Male contributor, age 40–49; the patient considered this a rash; the contributor reports the condition has been present for about one day; the lesion involves the leg; this image was taken at an angle; texture is reported as fluid-filled.
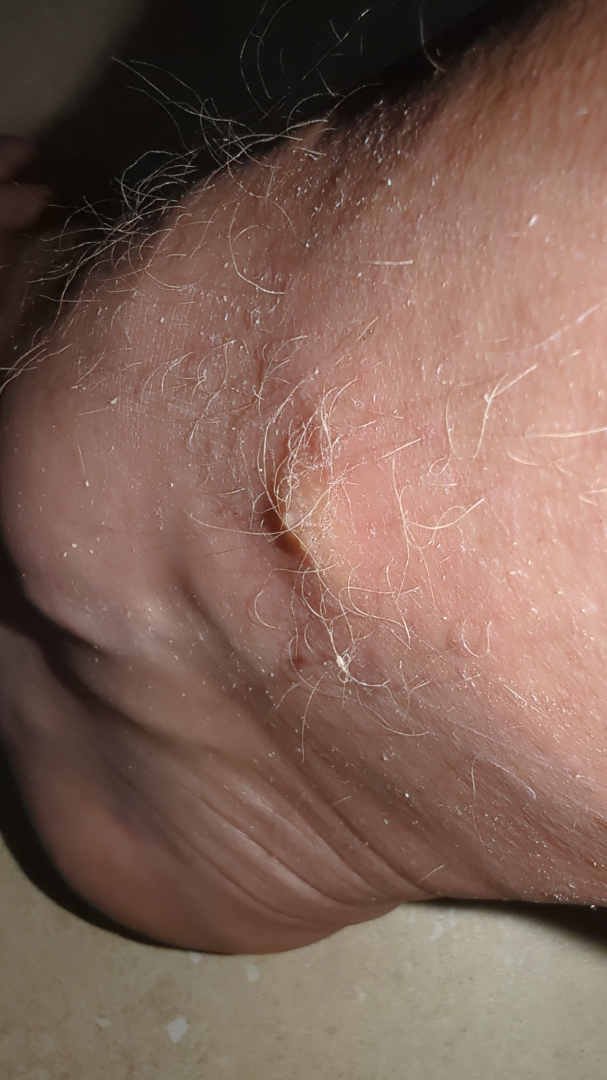On remote review of the image, most consistent with Insect Bite; less probable is Erythema migrans; lower on the differential is Impetigo; less likely is Drug Rash; a more distant consideration is Allergic Contact Dermatitis; a remote consideration is Abscess.